A dermoscopy image of a single skin lesion:
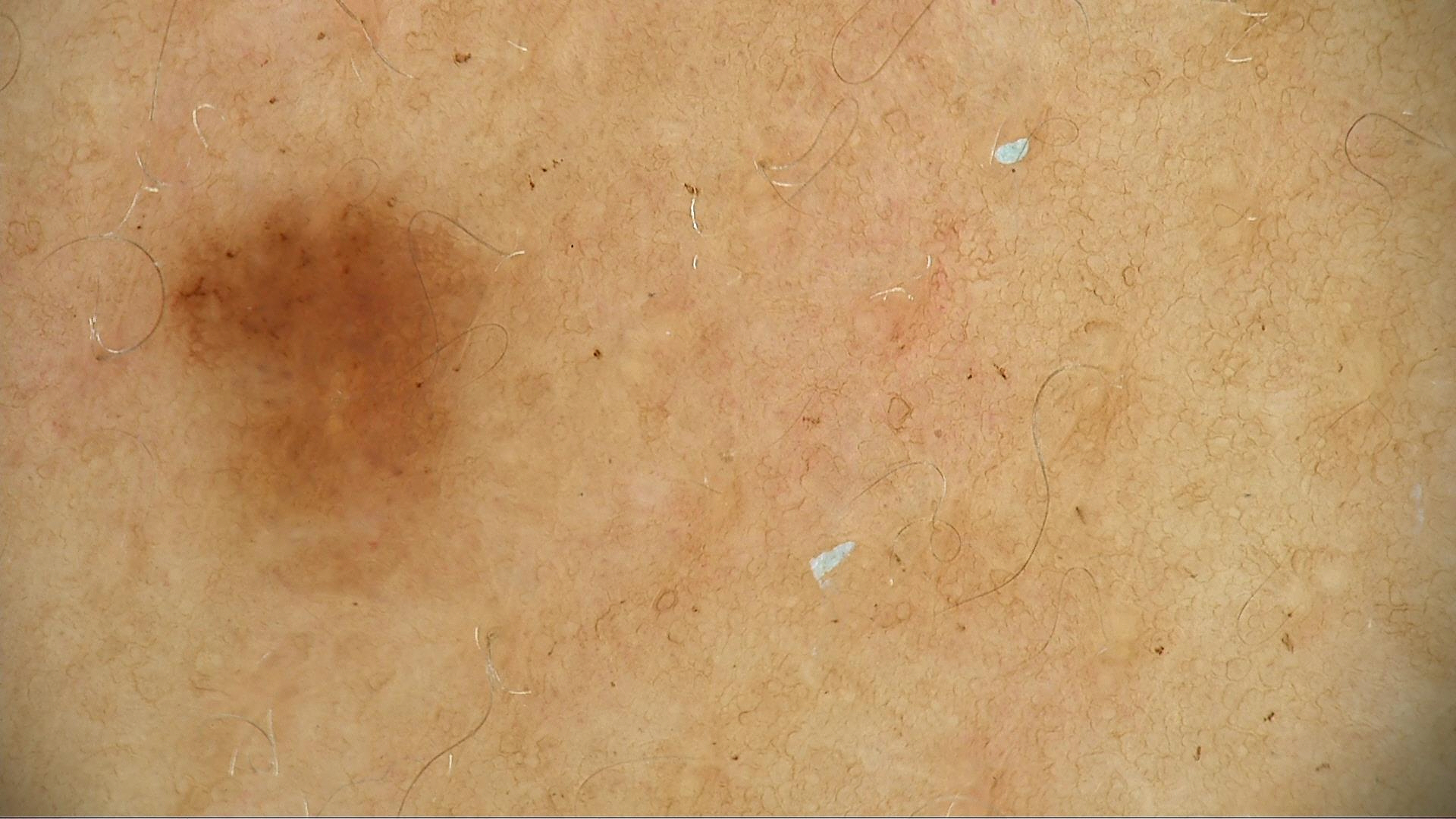Diagnosed as a dysplastic junctional nevus.